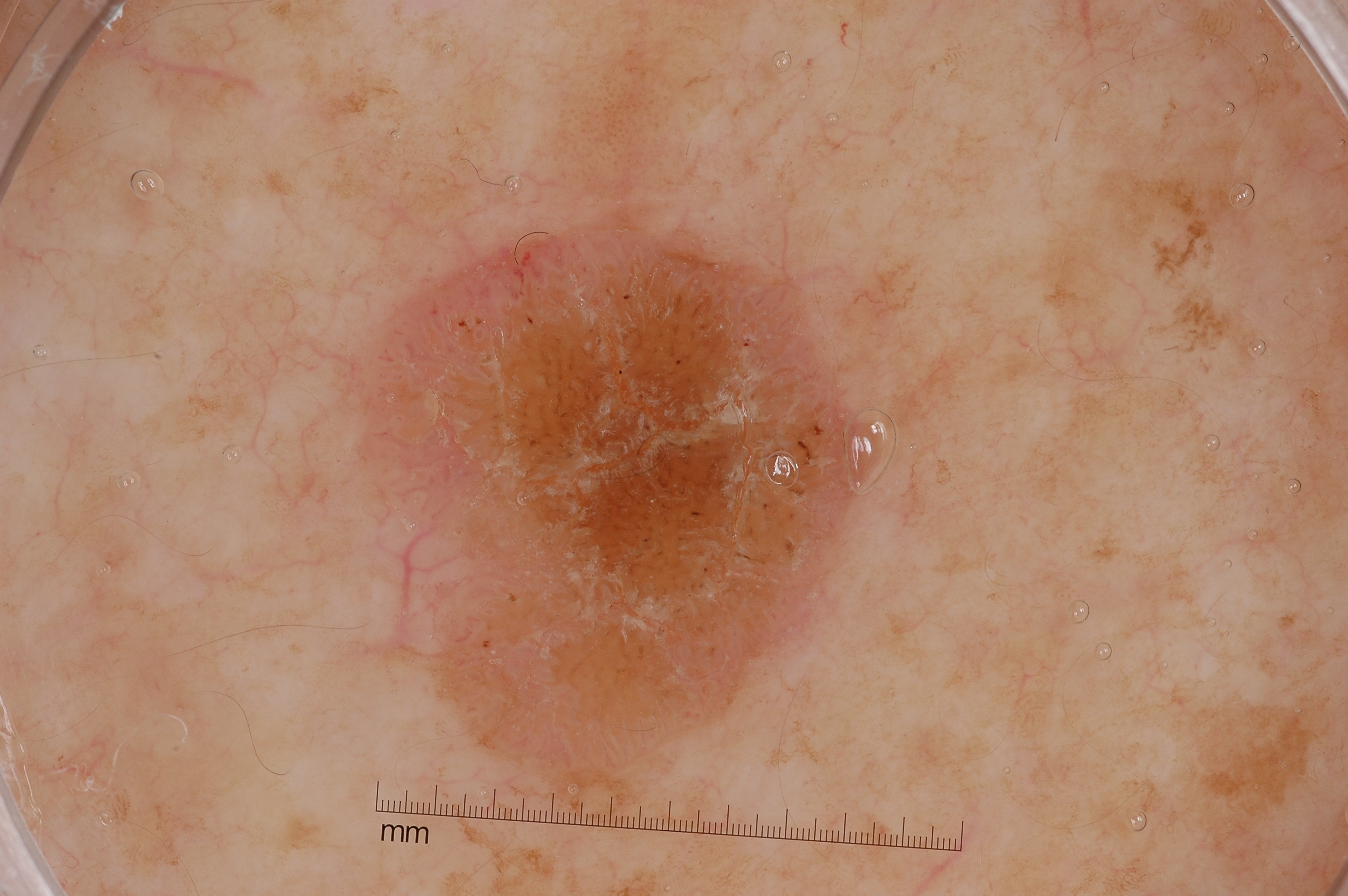Q: How was this image acquired?
A: dermoscopy of a skin lesion
Q: Who is the patient?
A: female, in their mid-70s
Q: Where is the lesion located?
A: 358/210/853/791
Q: What does dermoscopy show?
A: milia-like cysts
Q: What is this lesion?
A: a seborrheic keratosis, a benign skin lesion